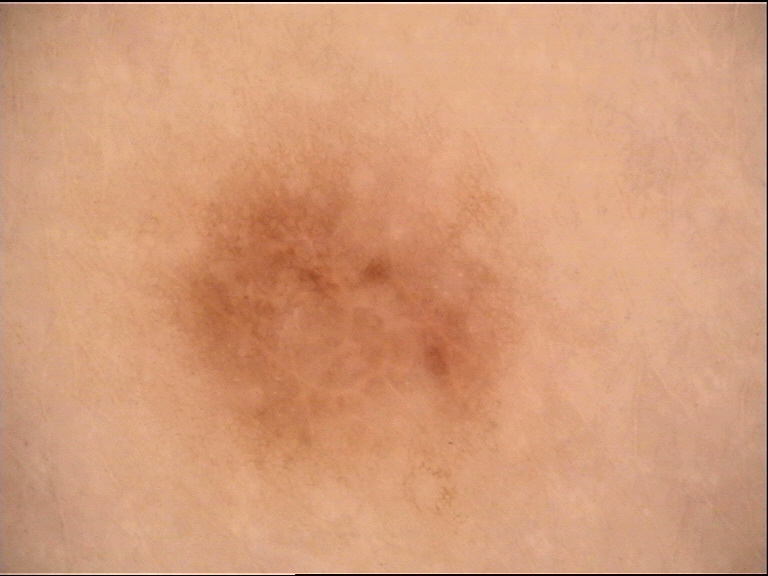assessment: junctional nevus (expert consensus).